Located on the leg, front of the torso, arm and back of the torso; an image taken at a distance; the patient is 18–29, female: 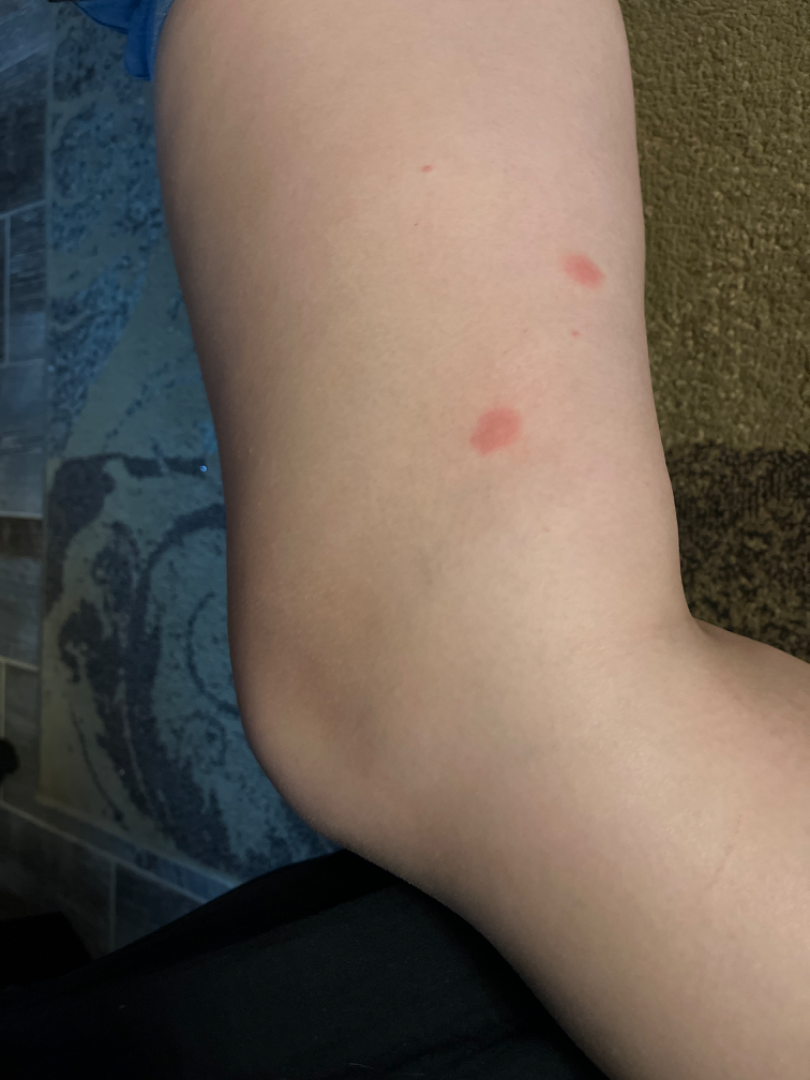Review: No differential diagnosis could be assigned on photographic review.